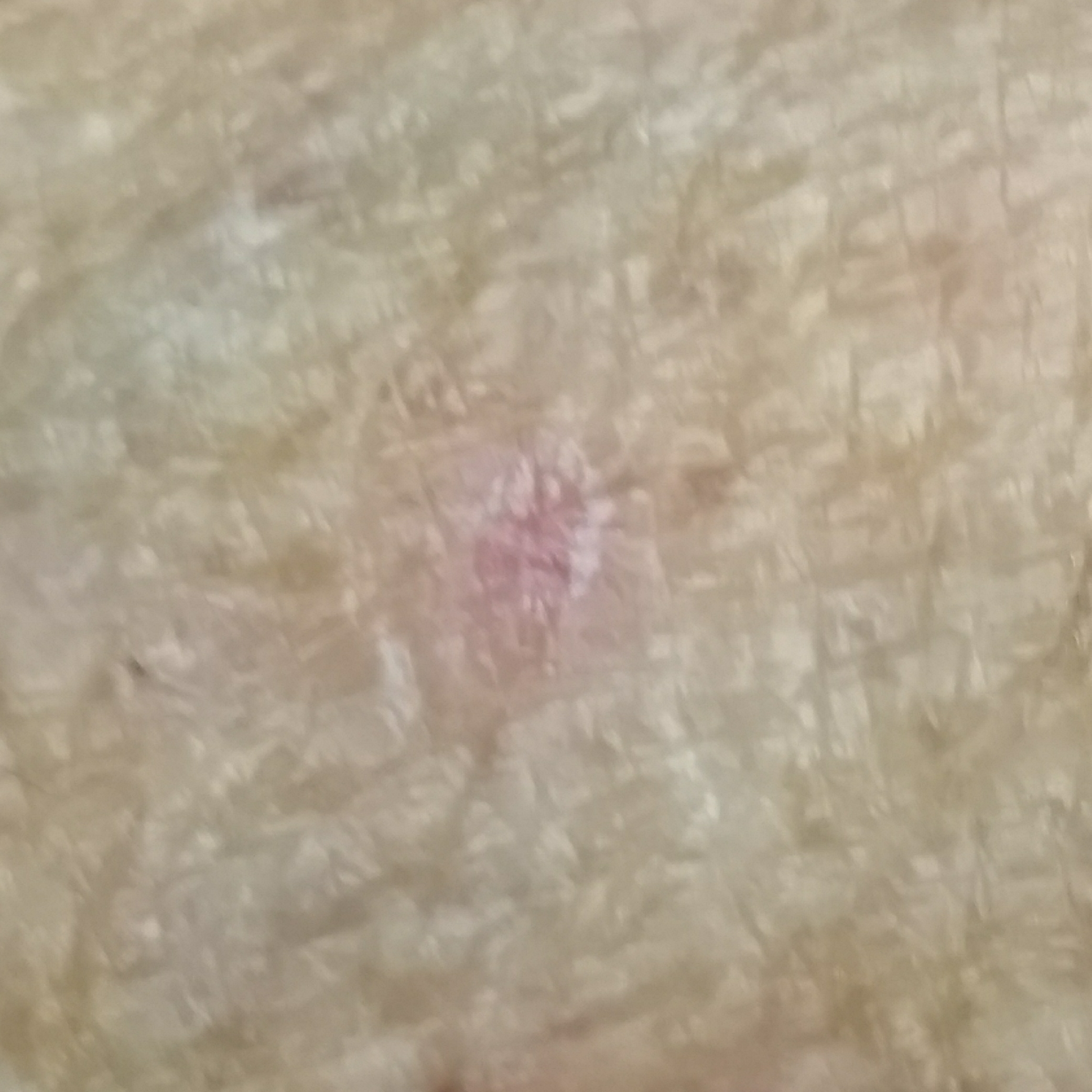Per patient report, the lesion itches, but has not changed and does not hurt.
Expert review favored an actinic keratosis.